The patient reports no personal history of skin cancer; a skin lesion imaged with a dermatoscope — 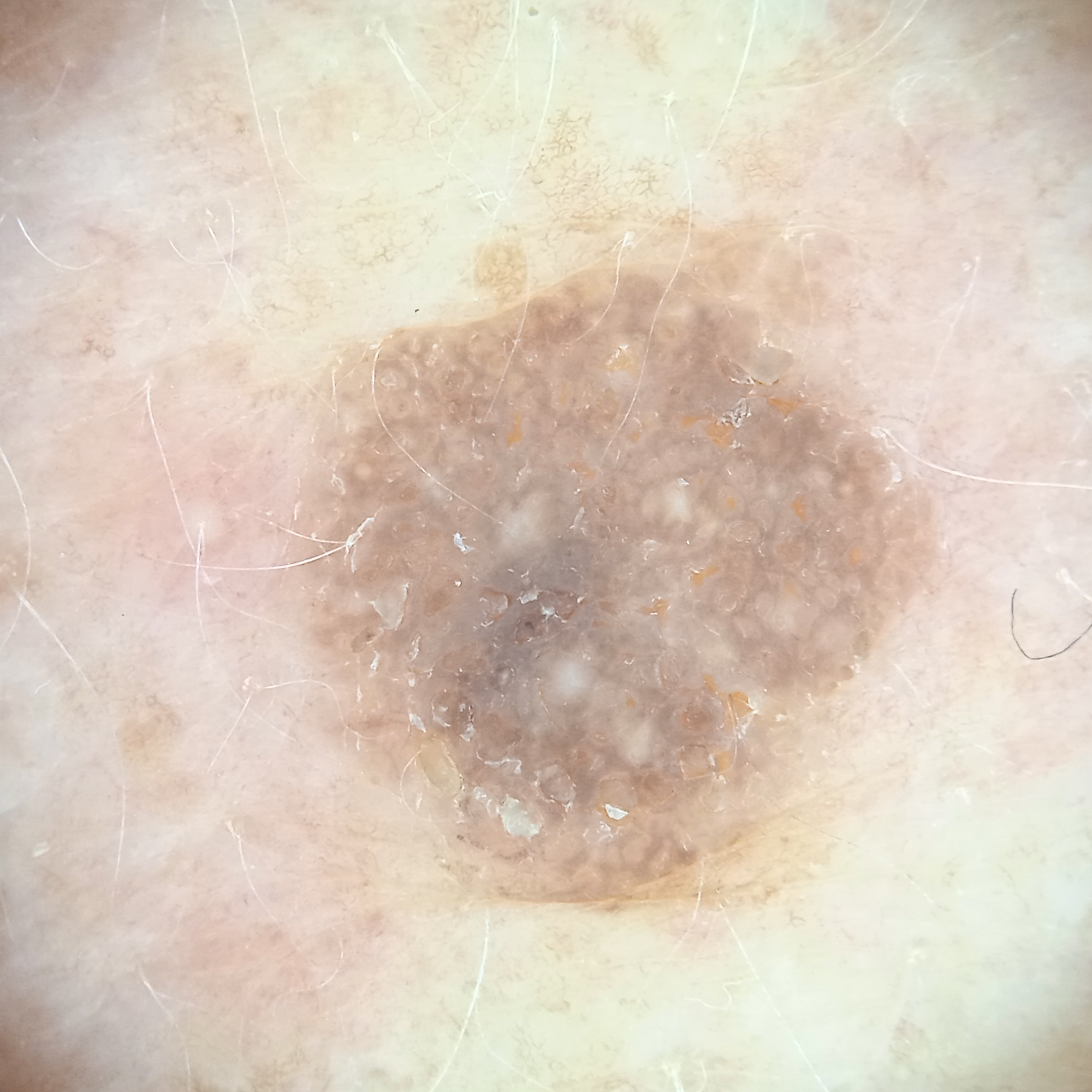Findings: The lesion involves the back. The lesion is about 7.3 mm across. Impression: The consensus diagnosis for this lesion was a seborrheic keratosis.